A skin lesion imaged with a dermatoscope: 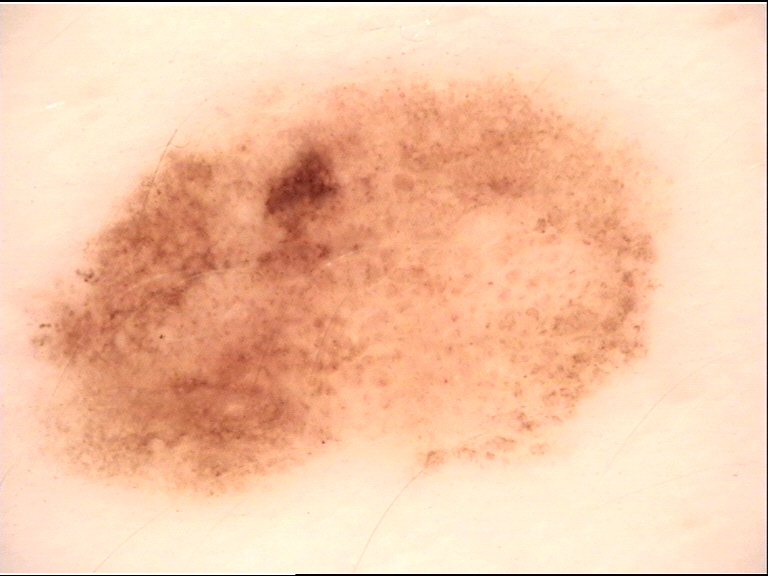Classified as a benign lesion — a dysplastic junctional nevus.